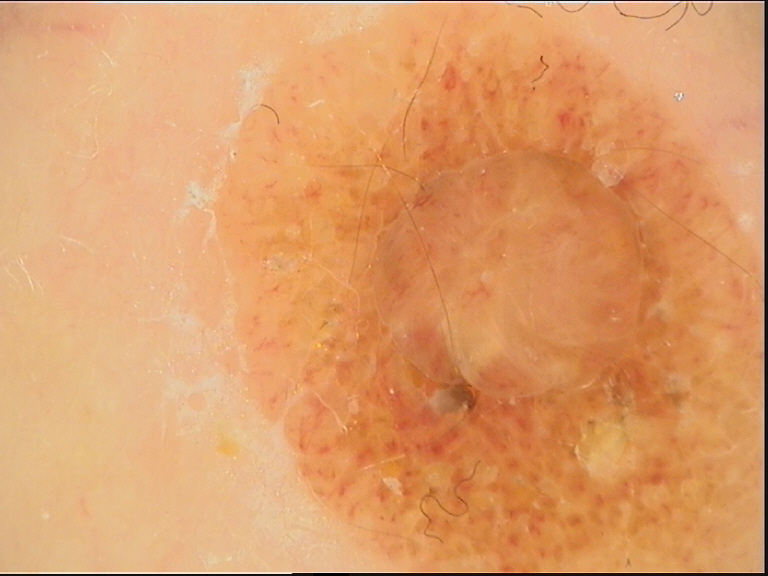Dermoscopy of a skin lesion. This is a banal lesion. Consistent with a dermal nevus.